A dermoscopy image of a single skin lesion:
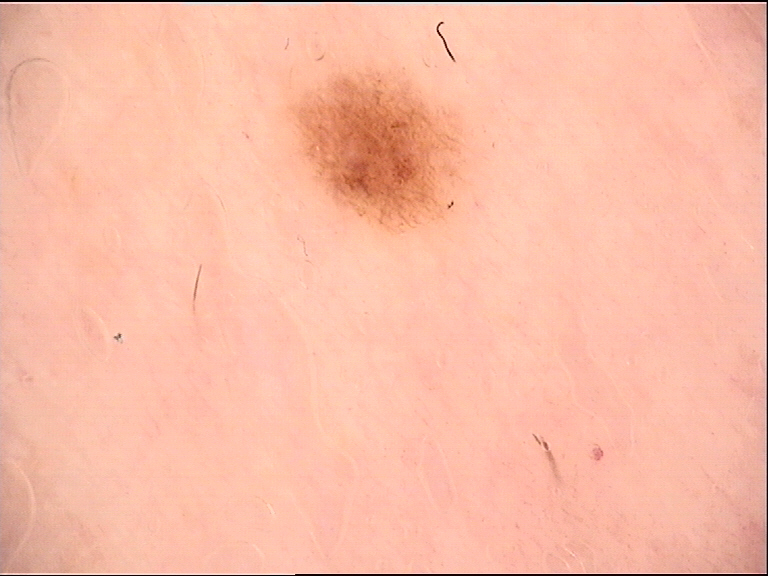diagnosis = dysplastic junctional nevus (expert consensus).